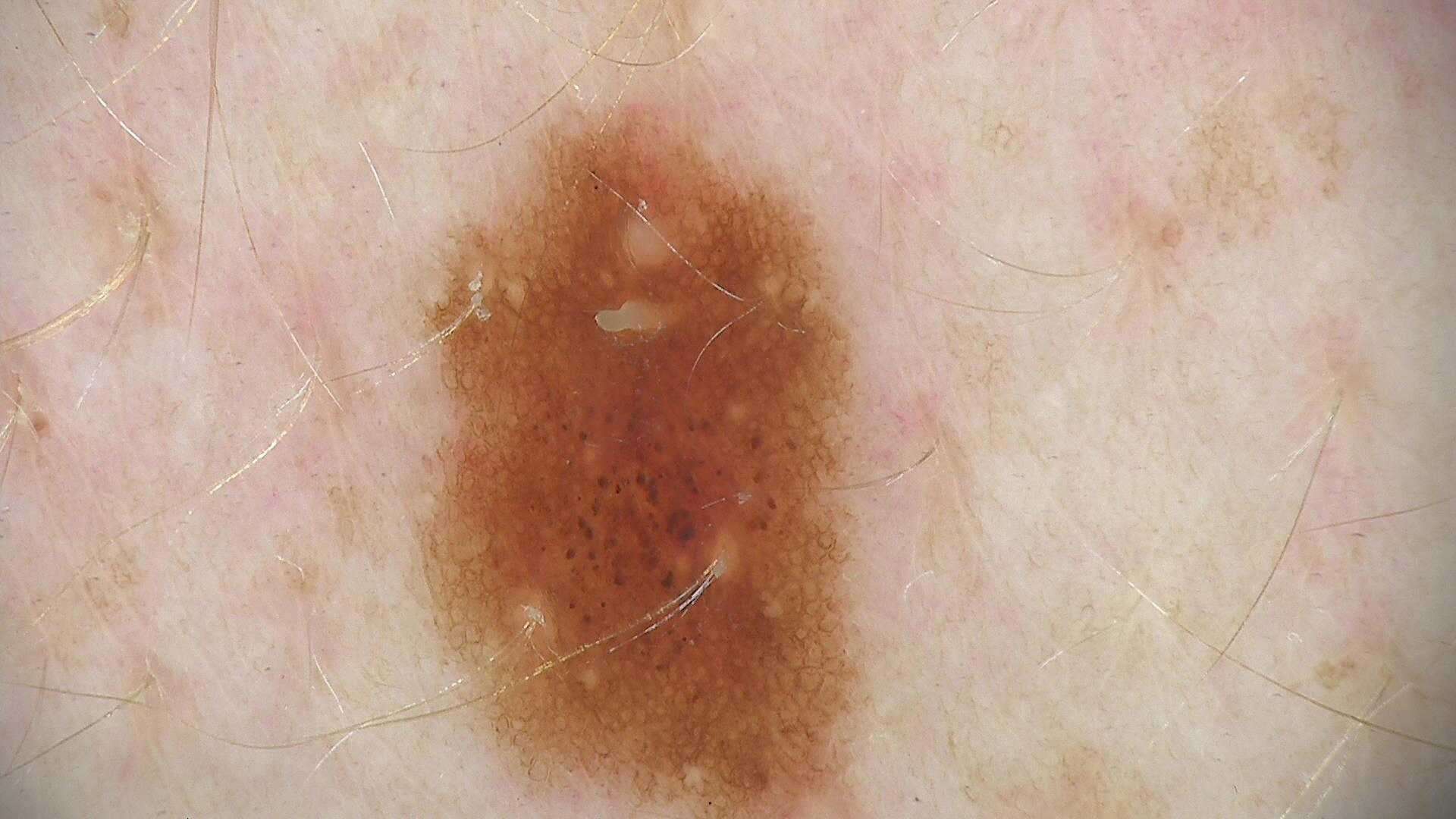modality: dermoscopy | diagnostic label: dysplastic junctional nevus (expert consensus).